A skin lesion imaged with a dermatoscope · a female subject, about 60 years old:
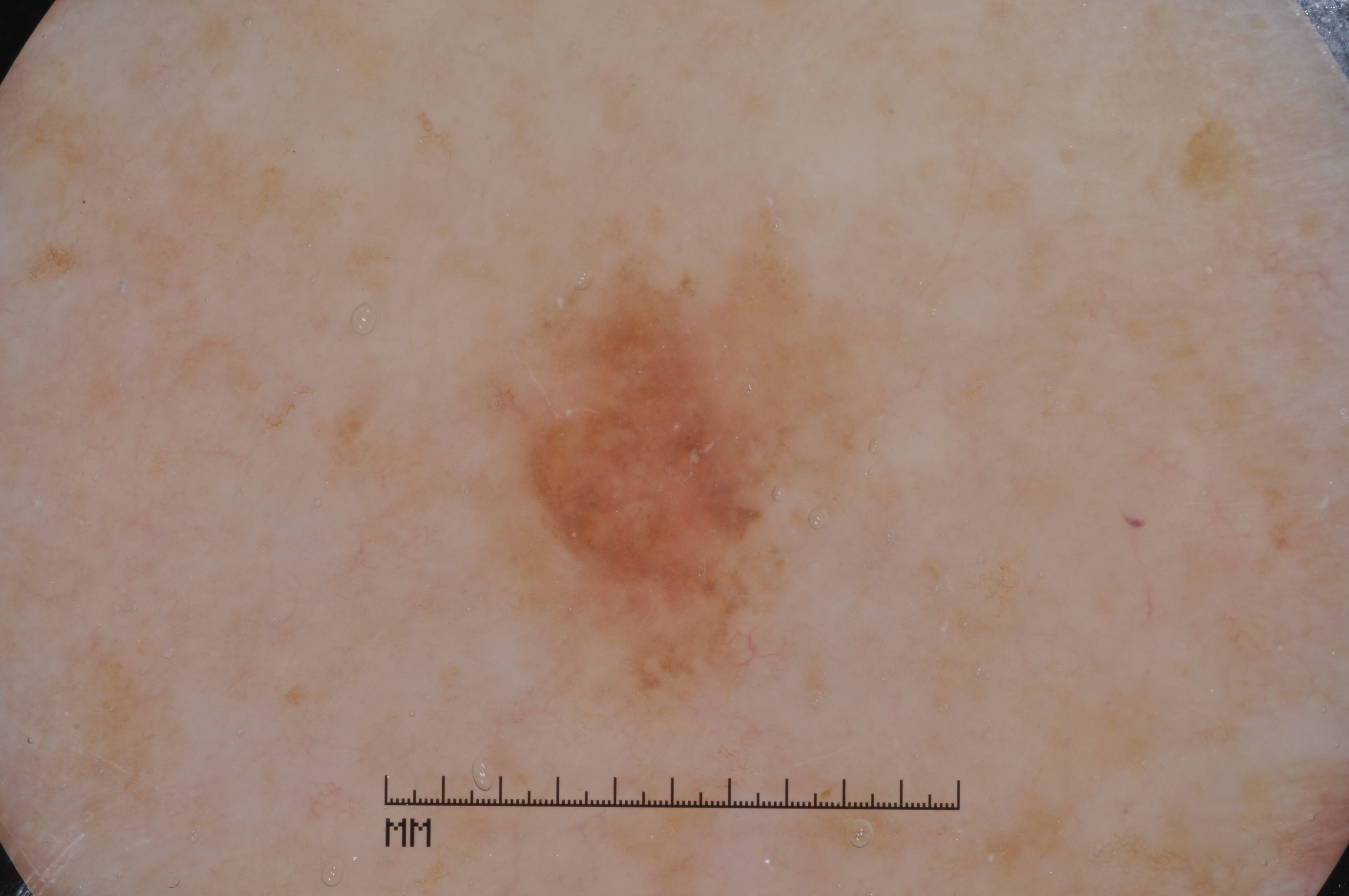Dermoscopically, the lesion shows milia-like cysts. As (left, top, right, bottom), lesion location: bbox(485, 259, 854, 700). Biopsy-confirmed as a melanoma, a malignant lesion.